A skin lesion imaged with a dermatoscope.
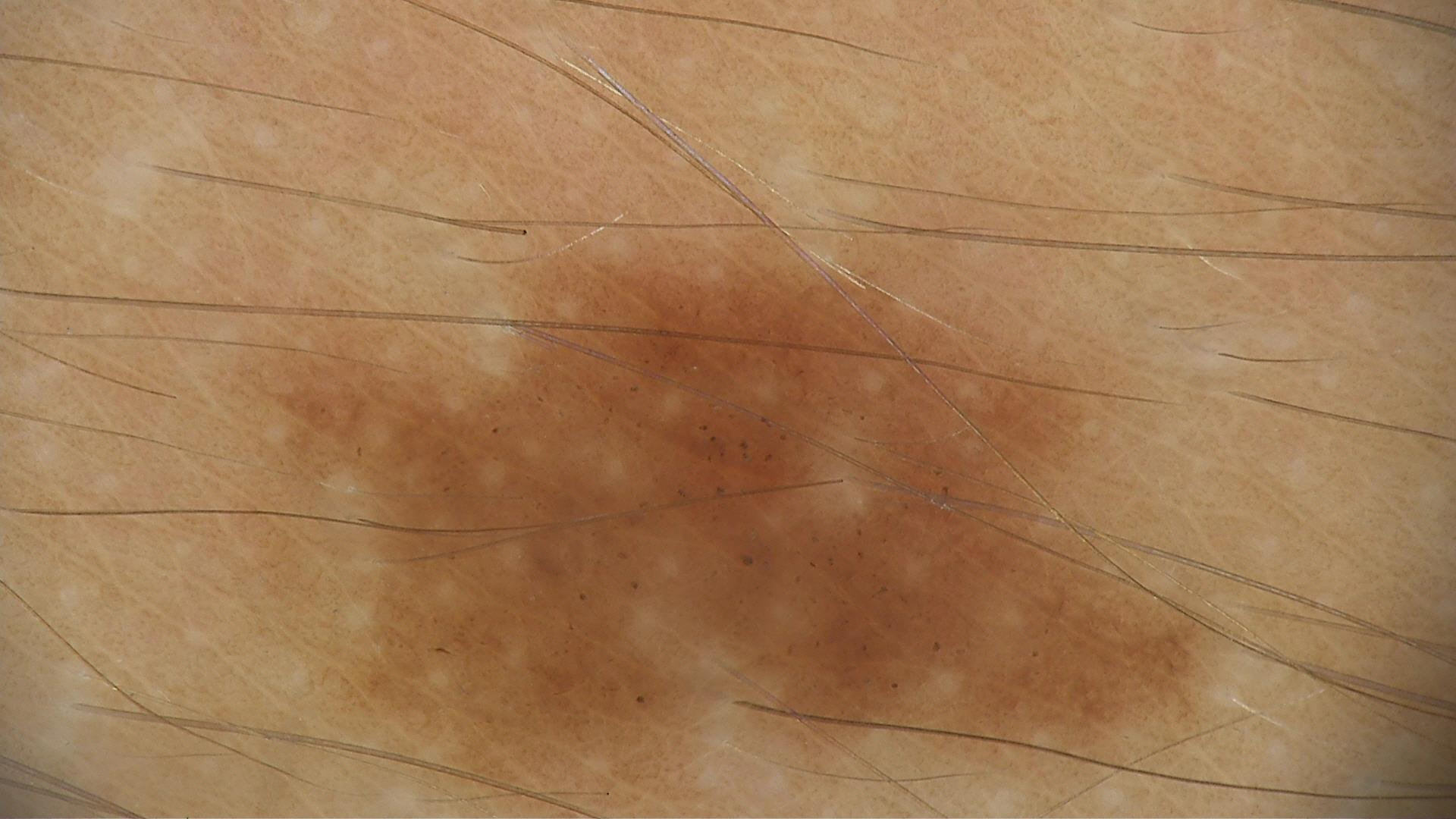diagnostic label: dysplastic junctional nevus (expert consensus)